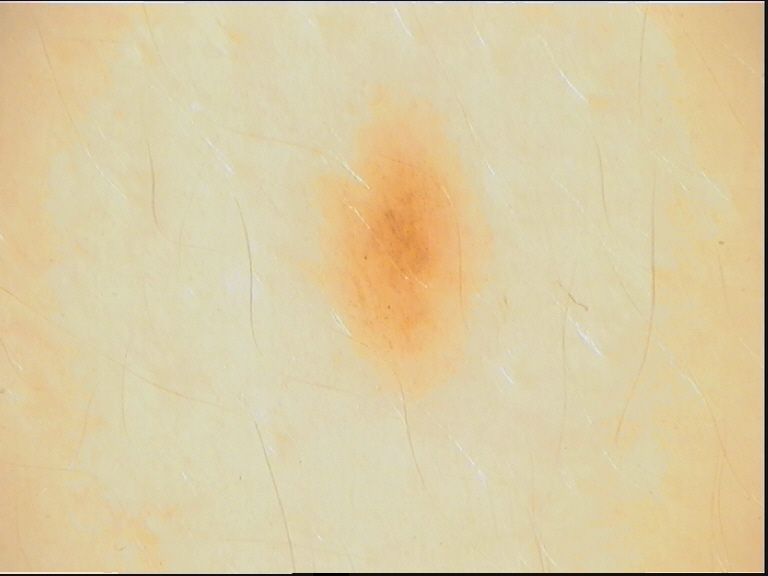image type: dermatoscopy | diagnostic label: dysplastic junctional nevus (expert consensus).